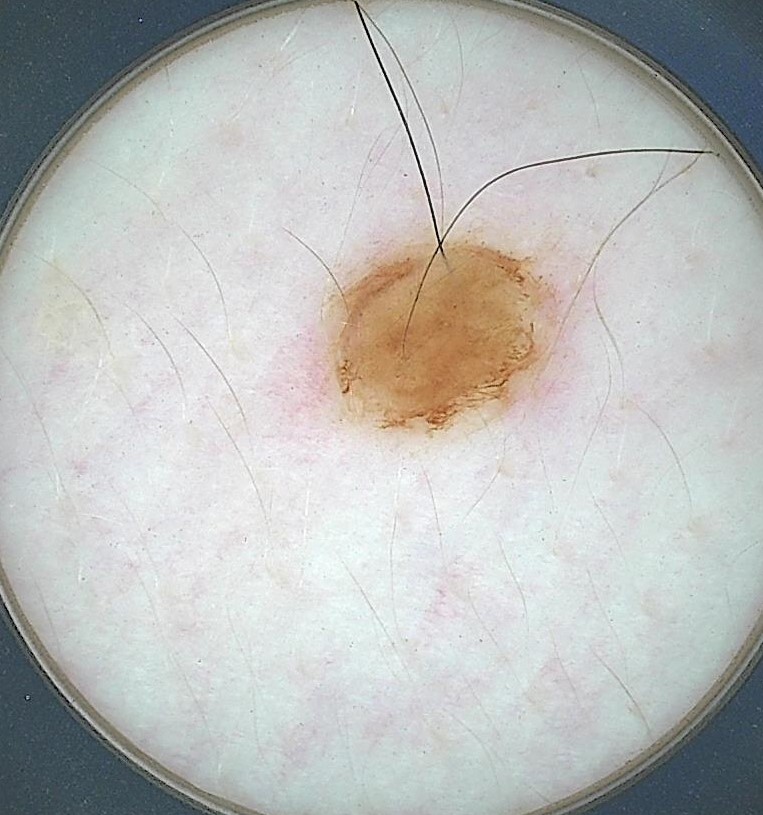  diagnosis:
    name: dermal nevus
    code: db
    malignancy: benign
    super_class: melanocytic
    confirmation: expert consensus